The lesion is described as raised or bumpy · this image was taken at a distance · the leg is involved:
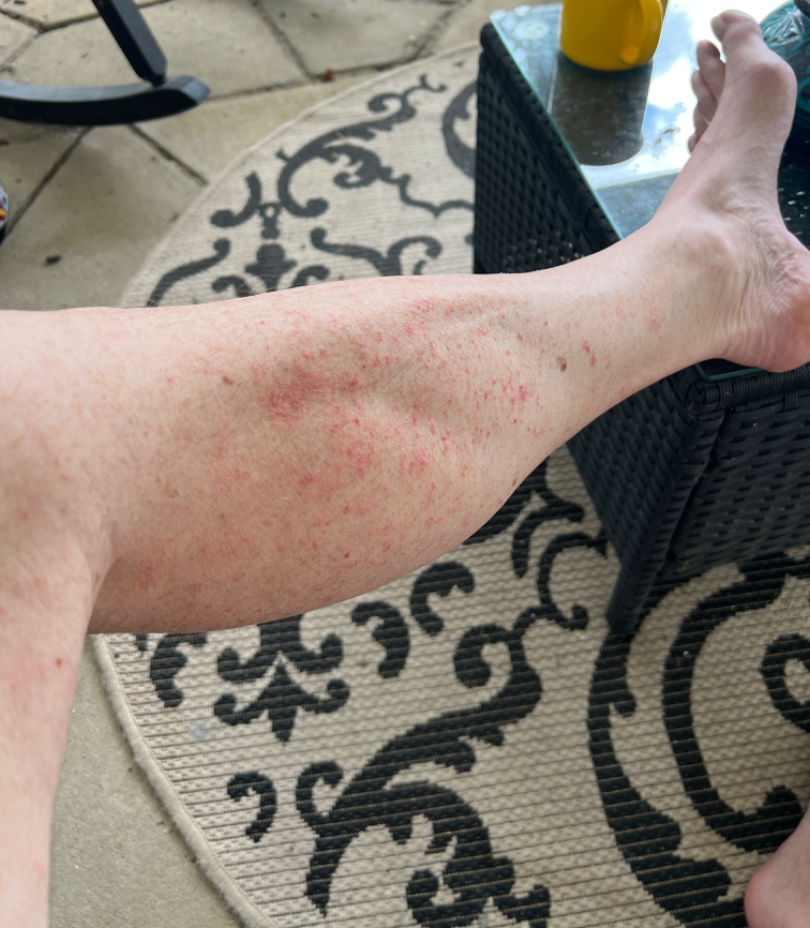Case summary:
* differential diagnosis: consistent with Acute dermatitis, NOS